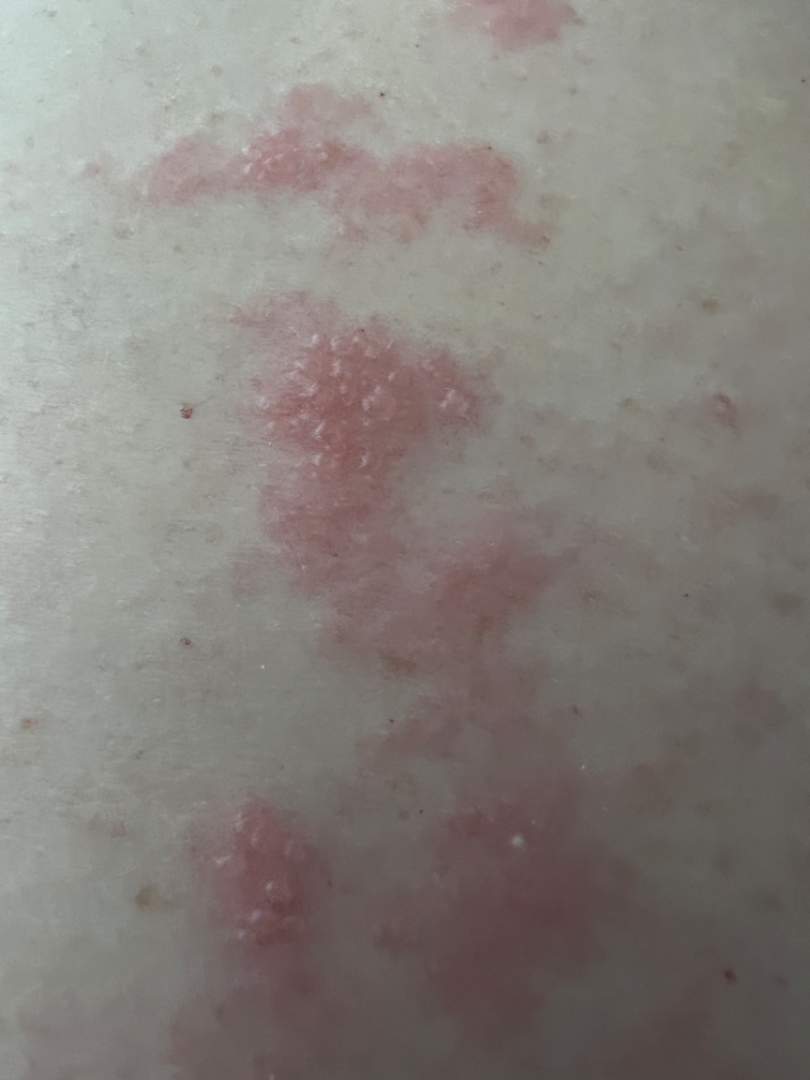The reviewer was unable to grade this case for skin condition.